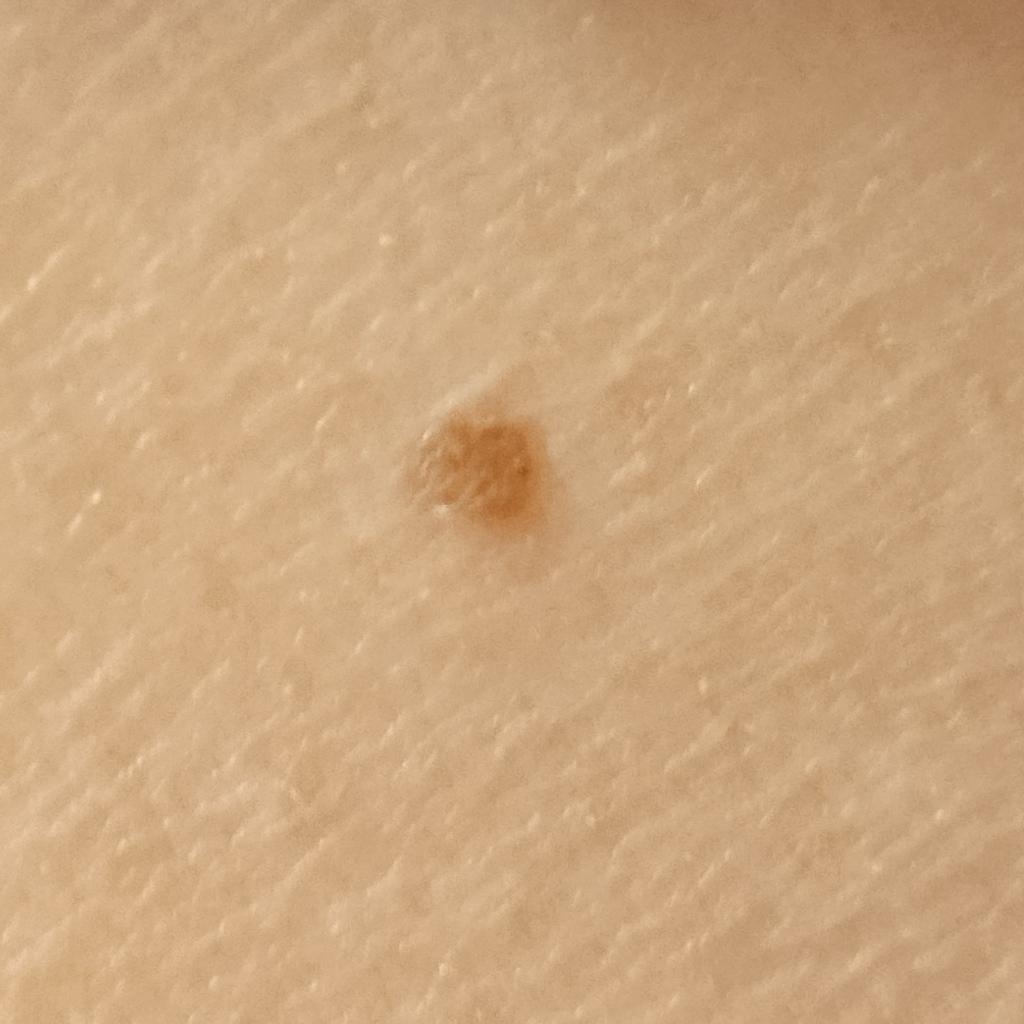| feature | finding |
|---|---|
| image | clinical photo |
| subject | female, aged 50 |
| nevus count | a moderate number of melanocytic nevi |
| sun reaction | skin reddens painfully with sun exposure |
| anatomic site | the back |
| lesion size | 2.2 mm |
| assessment | melanocytic nevus (dermatologist consensus) |